A dermoscopic photograph of a skin lesion · a female patient aged approximately 80:
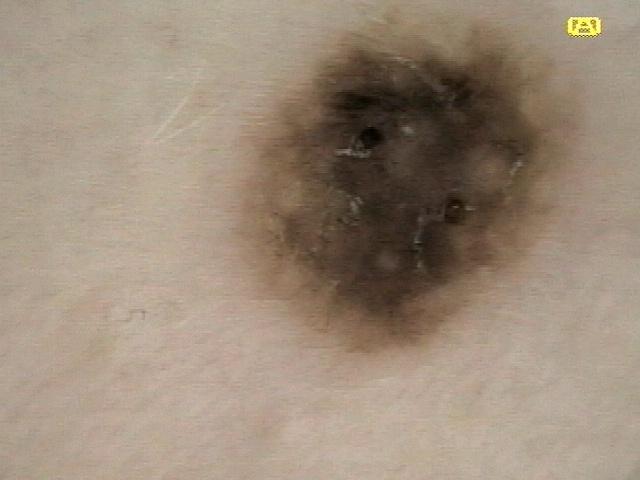Clinical context: The lesion is located on the trunk. Conclusion: The clinical impression was a seborrheic keratosis.